A clinical close-up photograph of a skin lesion; a subject age 61: 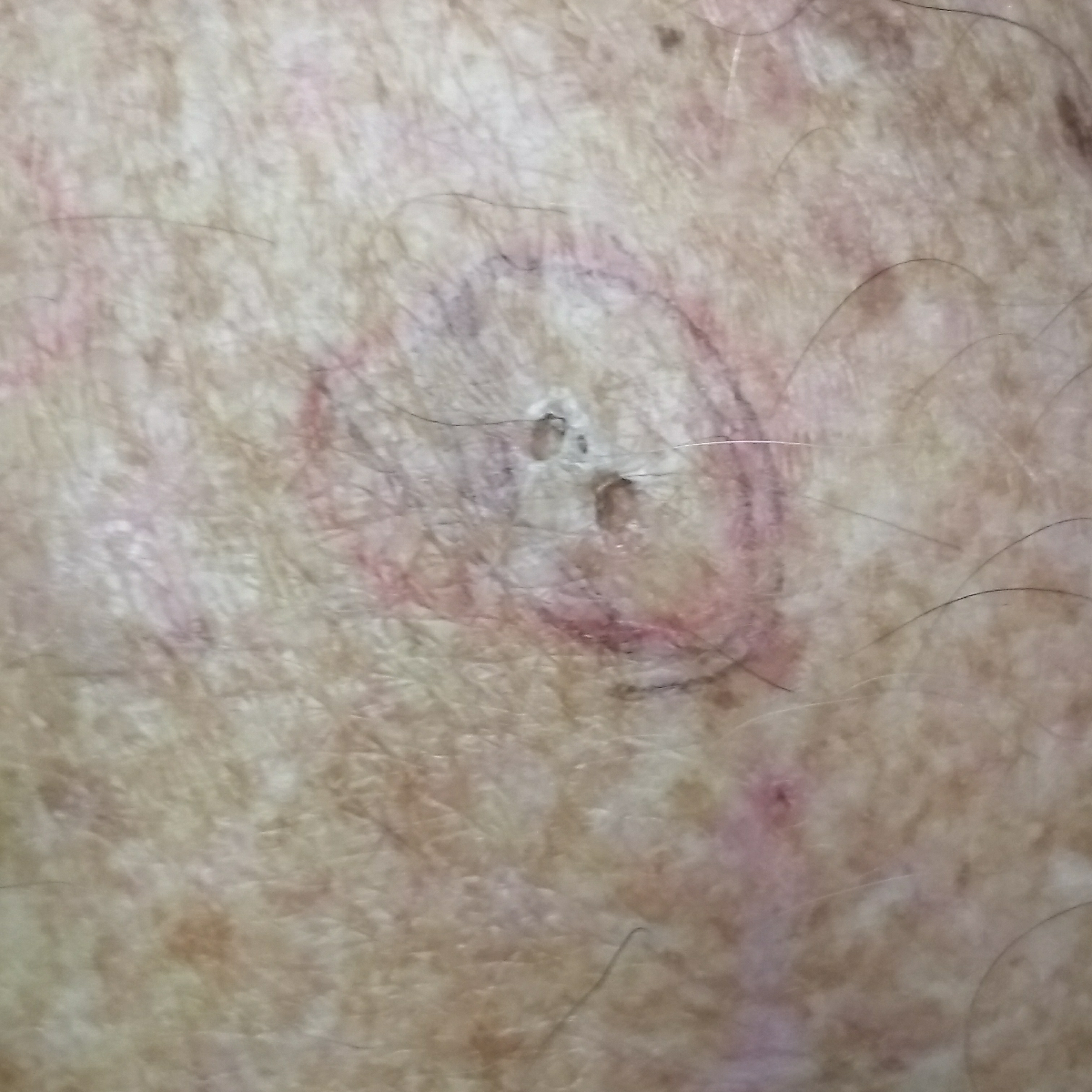The lesion is located on the chest. Clinically diagnosed as an actinic keratosis.